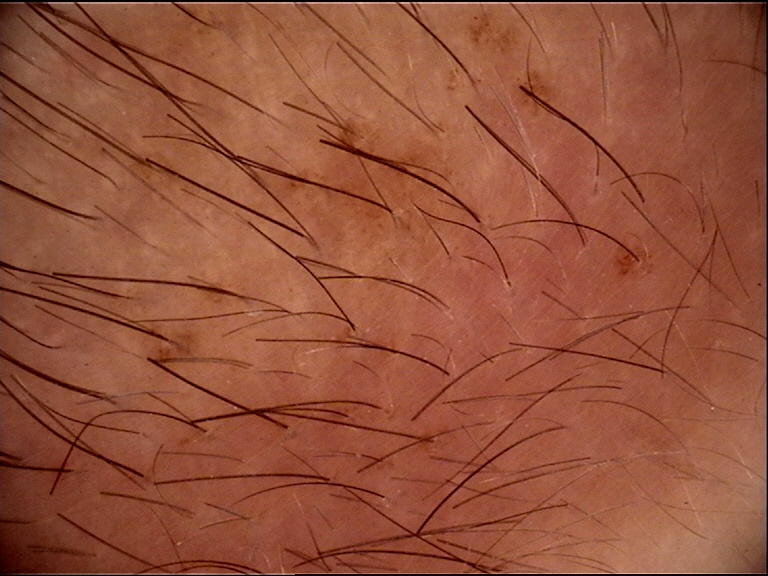assessment = congenital compound nevus (expert consensus).